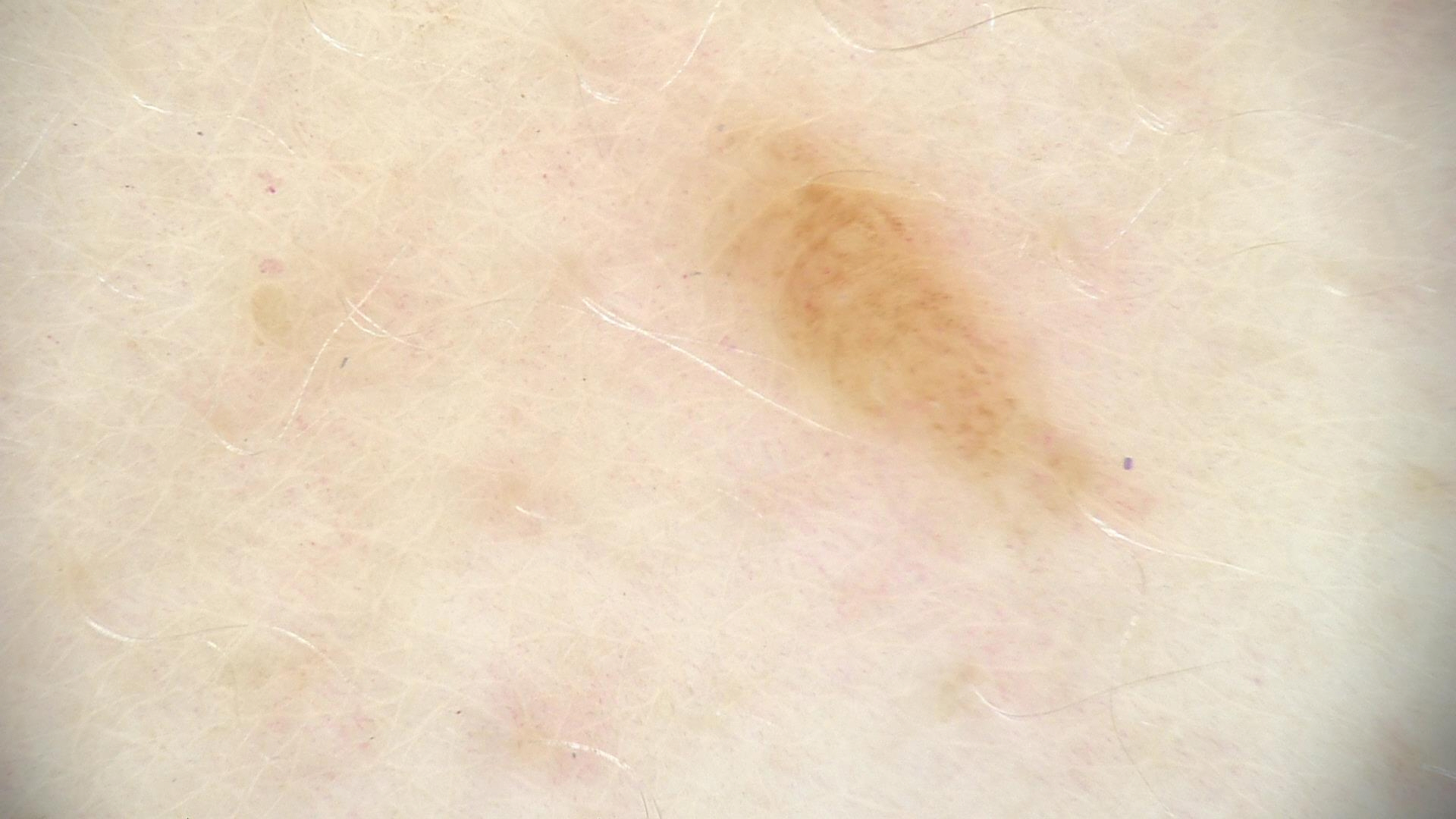Findings: A dermoscopy image of a single skin lesion. Impression: The diagnosis was a benign lesion — a dysplastic junctional nevus.